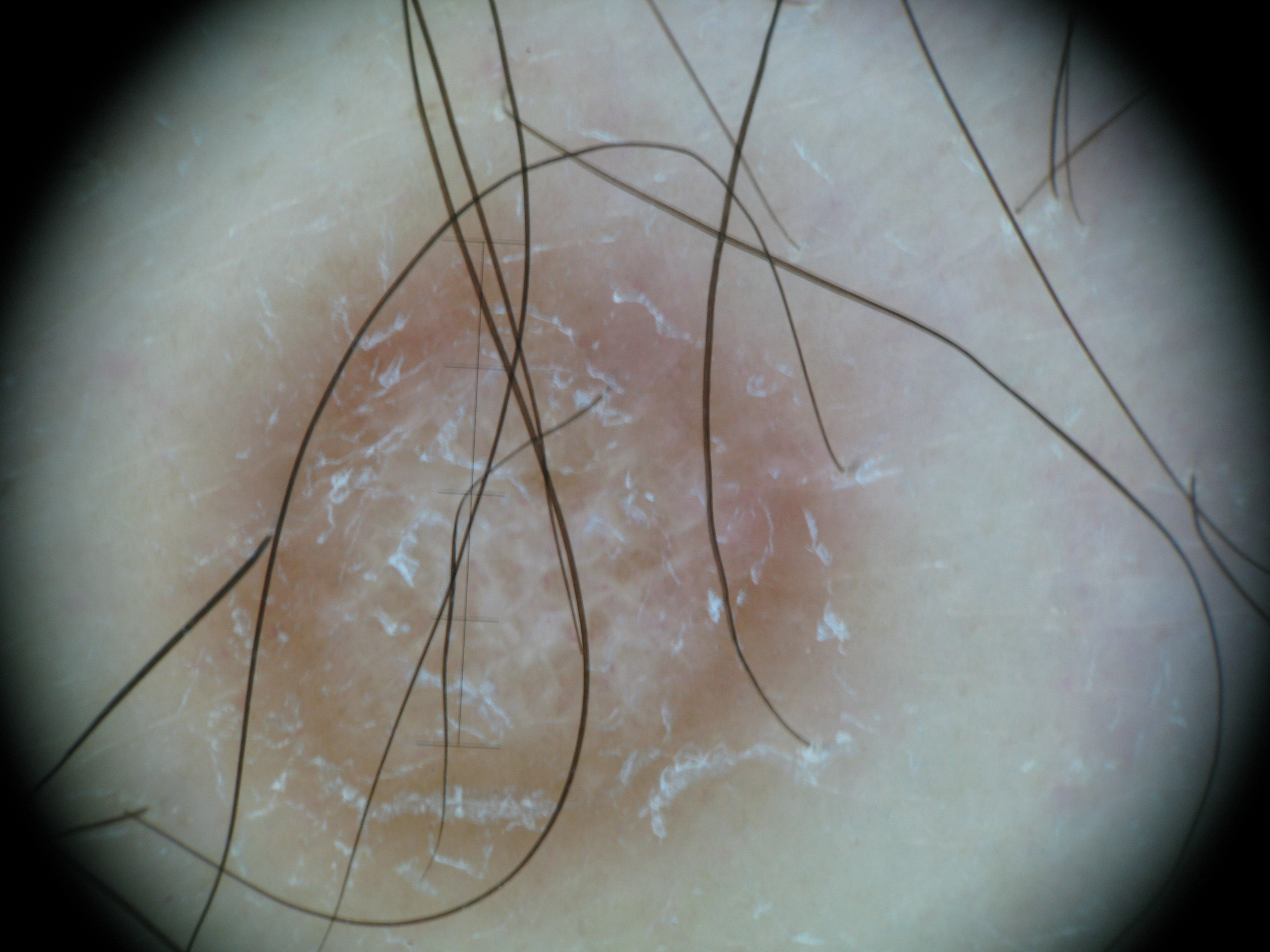lesion_type:
  main_class: fibro-histiocytic
diagnosis:
  name: dermatofibroma
  code: df
  malignancy: benign
  super_class: non-melanocytic
  confirmation: expert consensus